A dermoscopic photograph of a skin lesion:
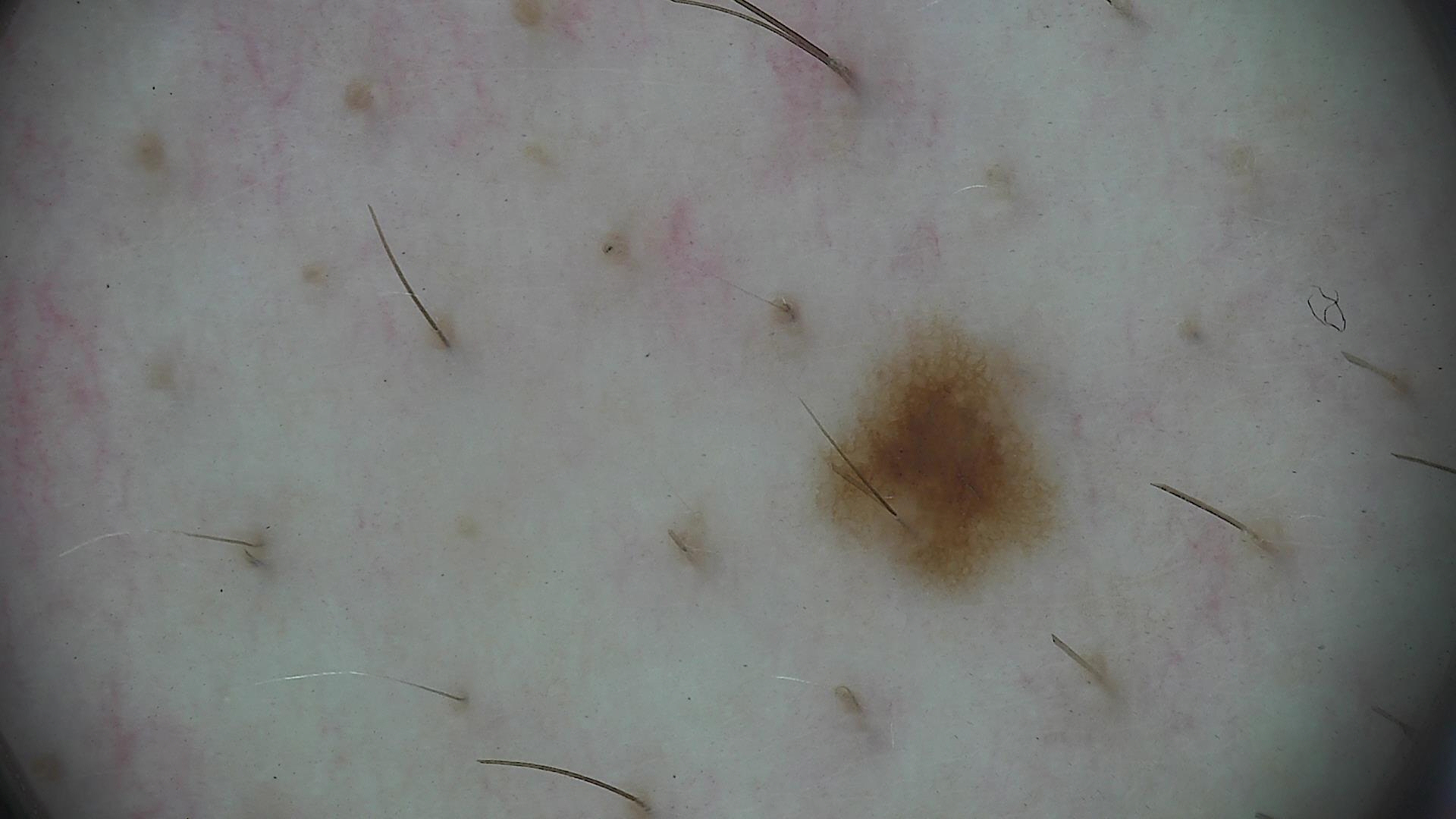| key | value |
|---|---|
| diagnostic label | dysplastic junctional nevus (expert consensus) |